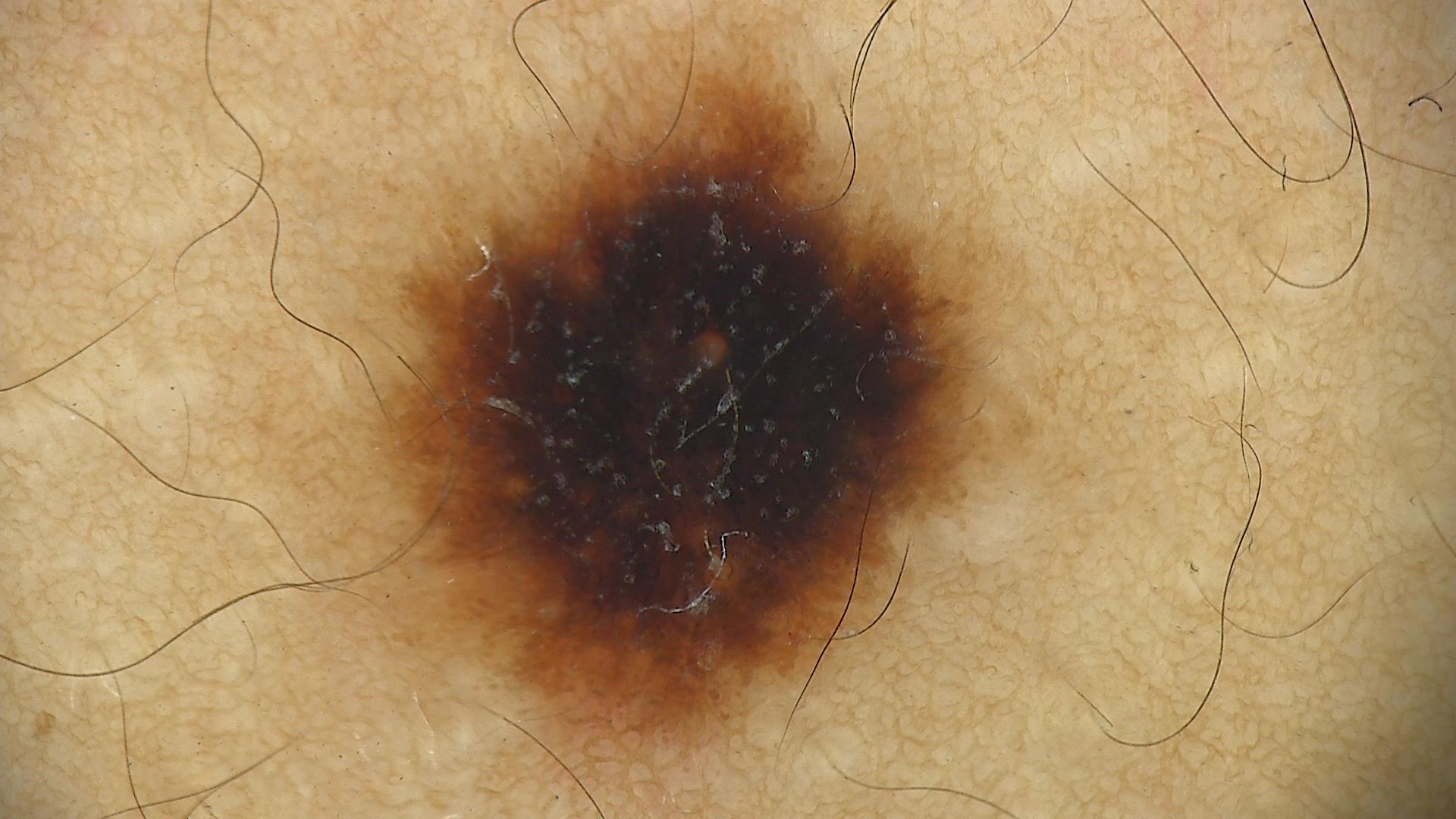A dermoscopic image of a skin lesion.
The diagnostic label was a benign lesion — a dysplastic junctional nevus.